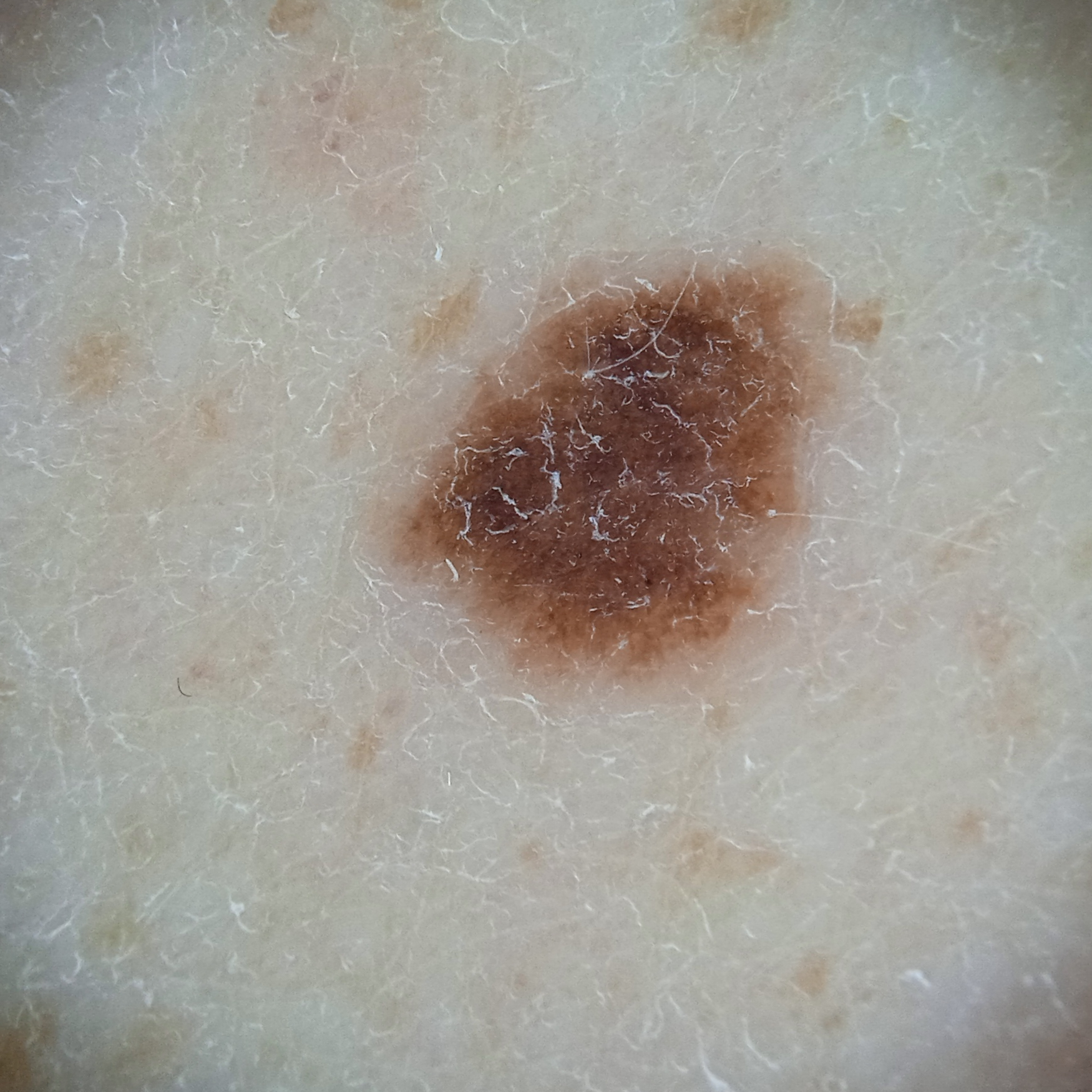Q: What was the diagnosis?
A: melanocytic nevus (dermatologist consensus)